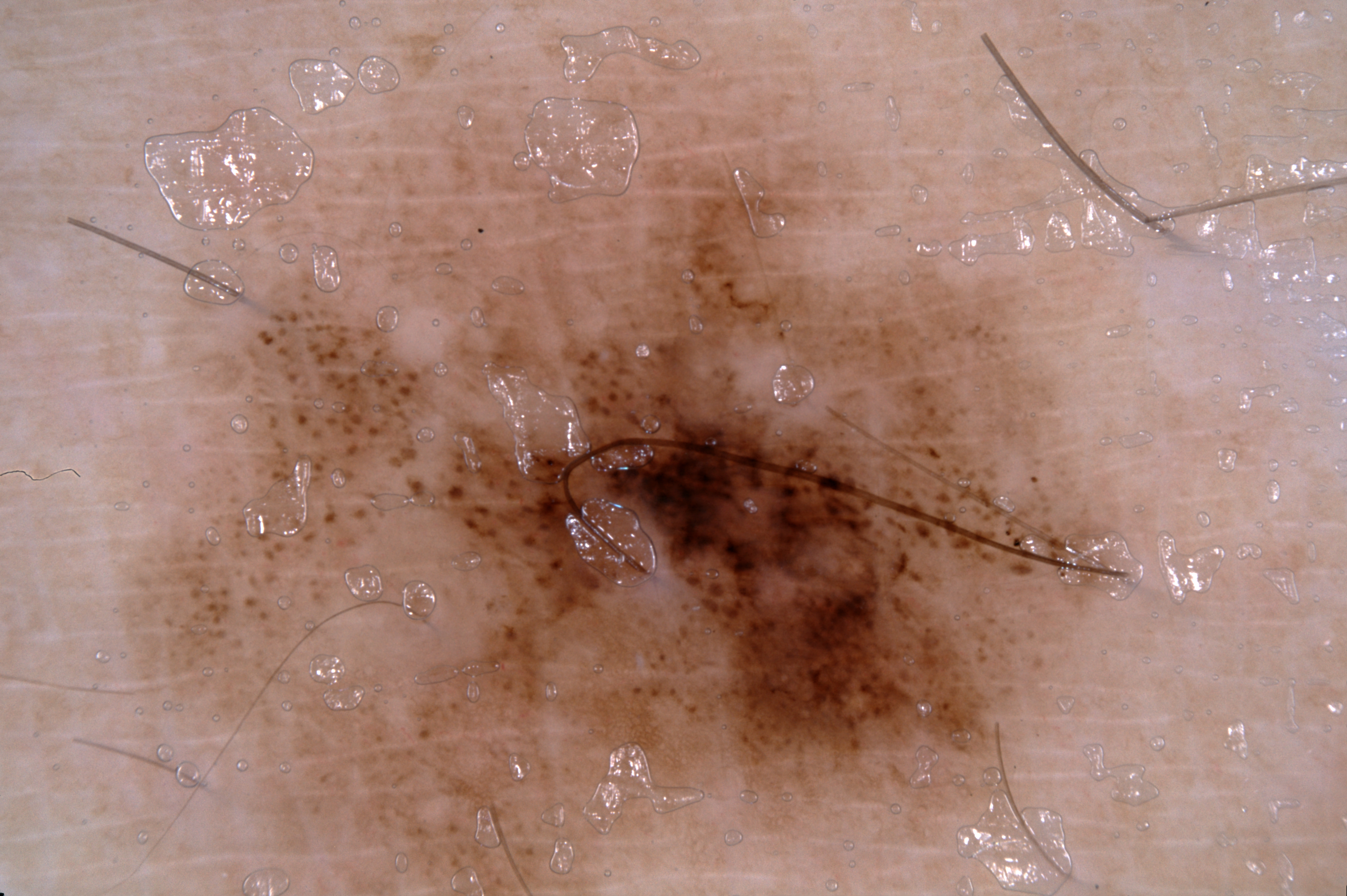Findings:
The subject is a male roughly 30 years of age. Dermoscopy of a skin lesion. A large lesion occupying much of the field. The lesion reaches the border of the frame. In (x1, y1, x2, y2) order, the lesion occupies the region 137/84/1115/895. Dermoscopic assessment notes pigment network.
Diagnosis:
Histopathologically confirmed as a melanoma.